Located on the arm and head or neck. The photo was captured at an angle:
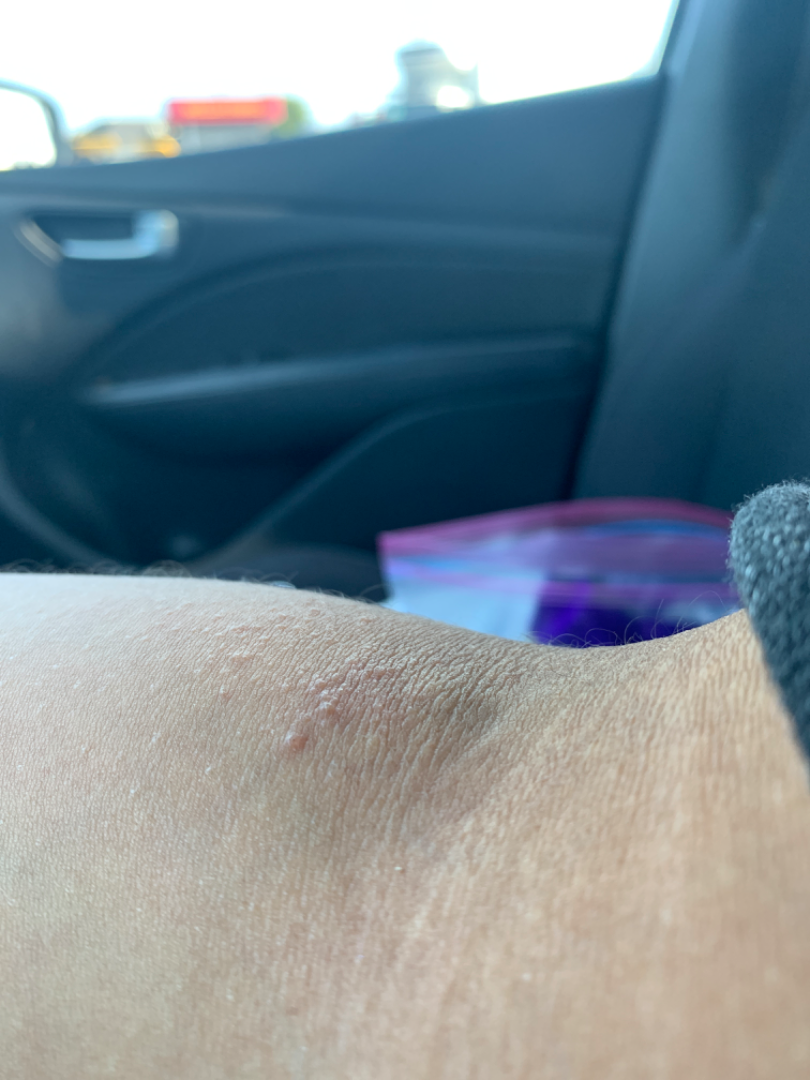differential diagnosis = single-reviewer assessment: favoring Lichen Simplex Chronicus; possibly Acanthosis nigricans; with consideration of PXE (pseudoxanthoma elasticum) like syndrome.